A skin lesion imaged with a dermatoscope.
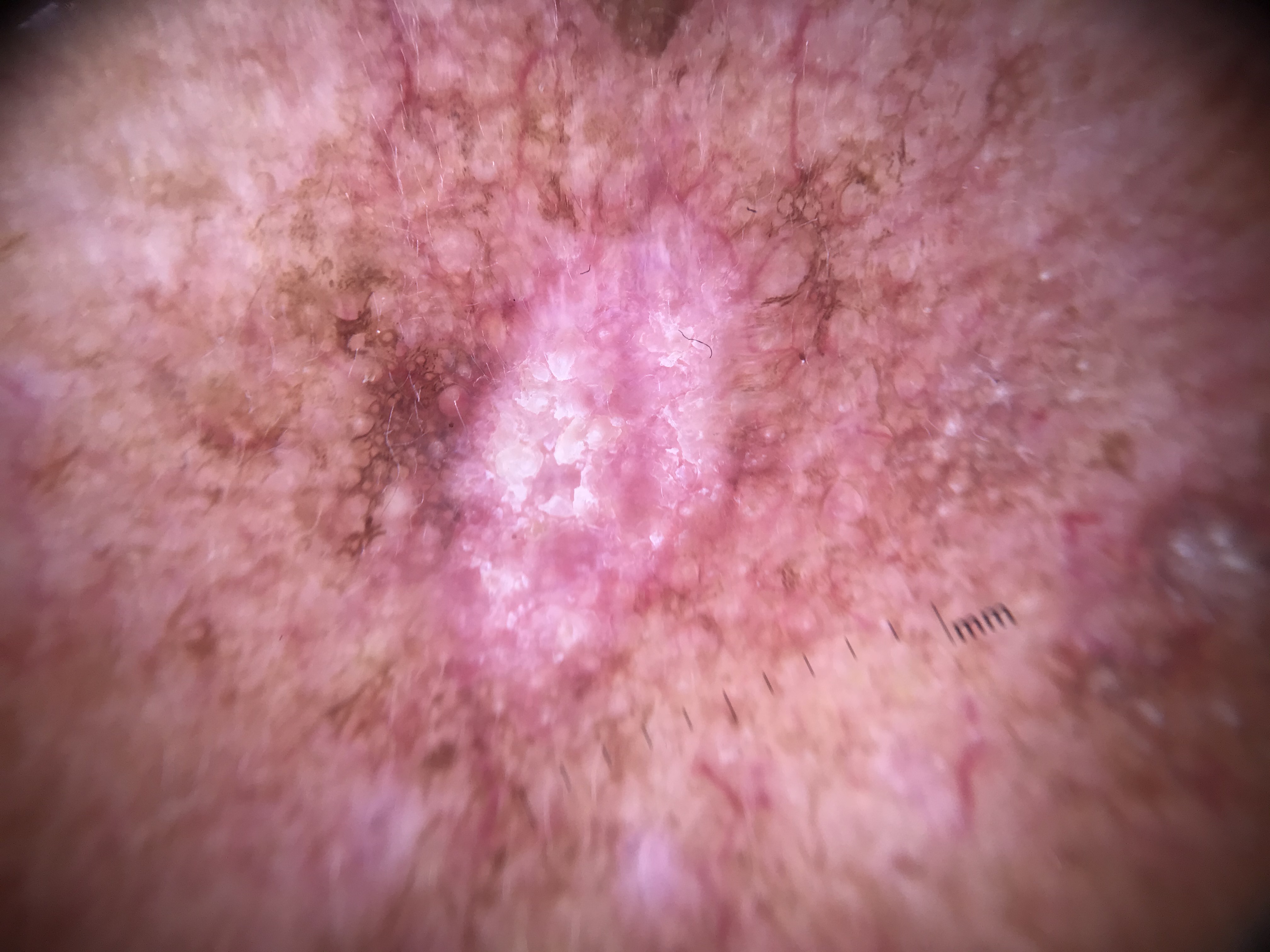Summary: This is a keratinocytic lesion. Conclusion: Biopsy-confirmed as a squamous cell carcinoma.